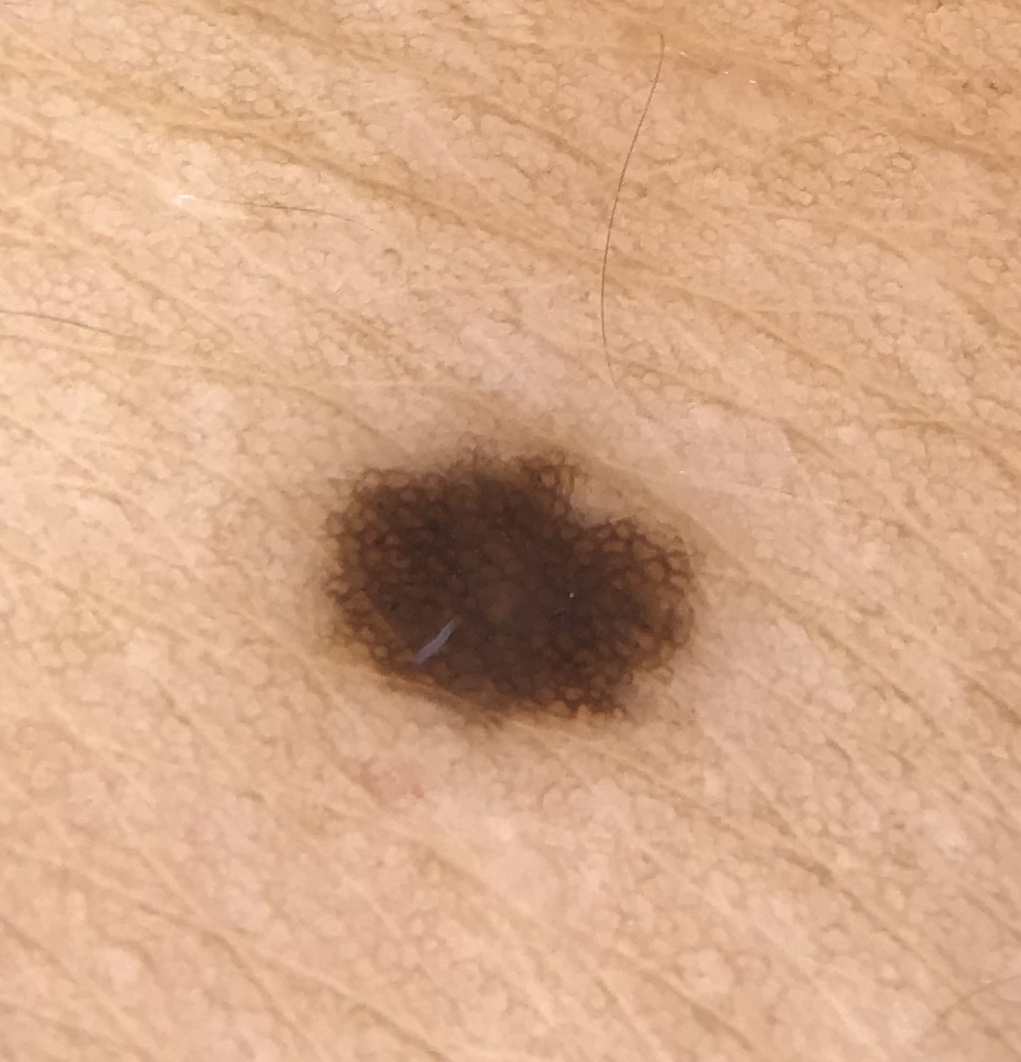<dermoscopy>
  <image>dermatoscopy</image>
  <diagnosis>
    <name>junctional nevus</name>
    <code>jb</code>
    <malignancy>benign</malignancy>
    <super_class>melanocytic</super_class>
    <confirmation>expert consensus</confirmation>
  </diagnosis>
</dermoscopy>